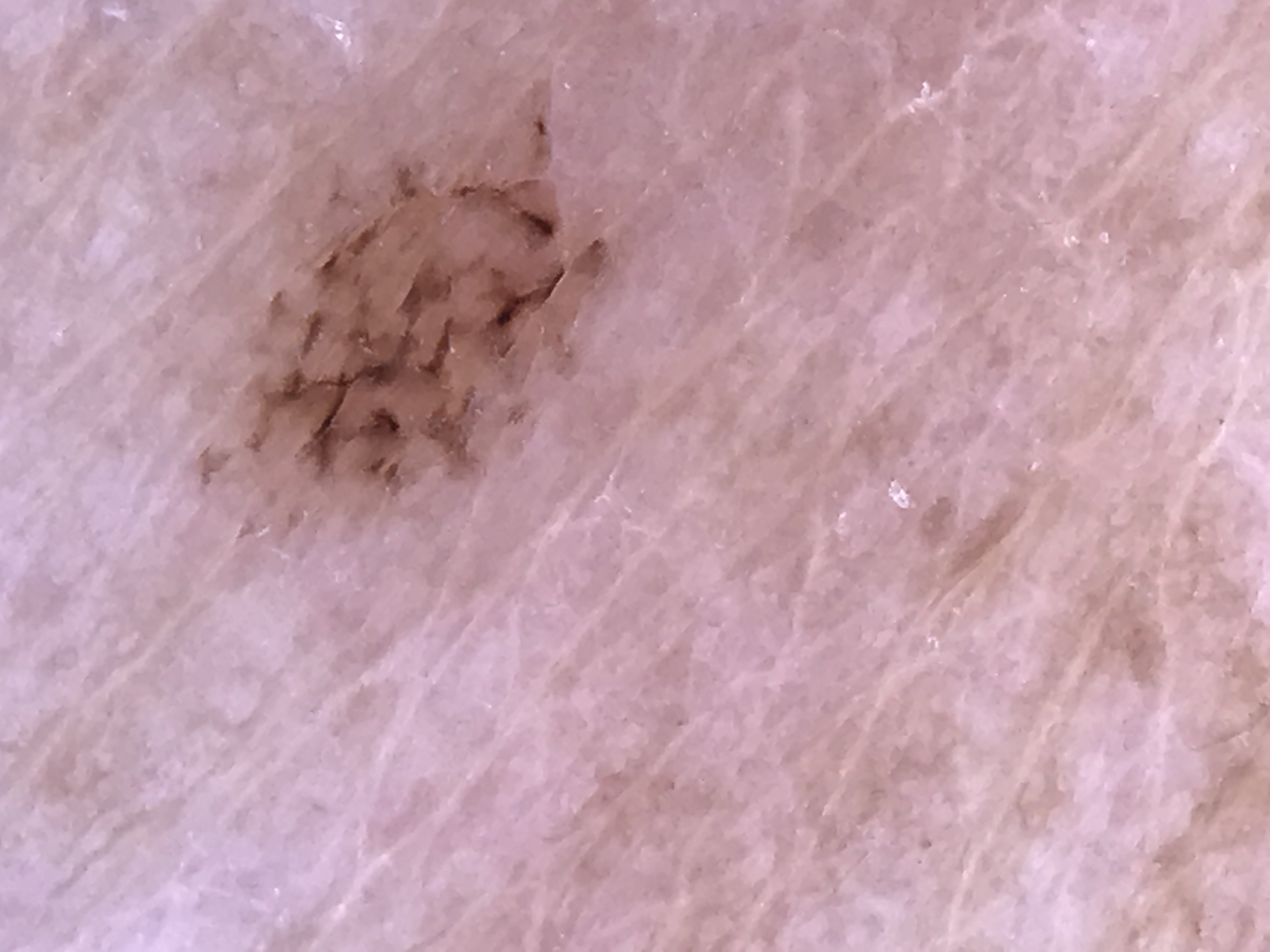image type = dermoscopy | diagnosis = acral dysplastic junctional nevus (expert consensus).